A female patient aged 58-62 — 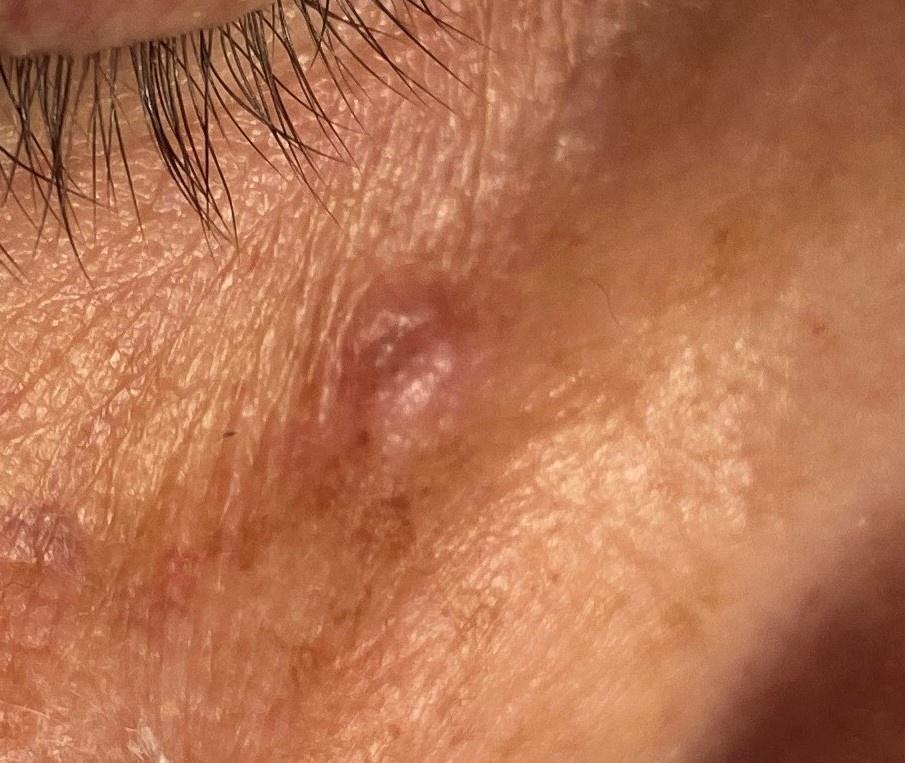Q: Where is the lesion located?
A: the head or neck
Q: What is this lesion?
A: Basal cell carcinoma (biopsy-proven)